The photo was captured at an angle:
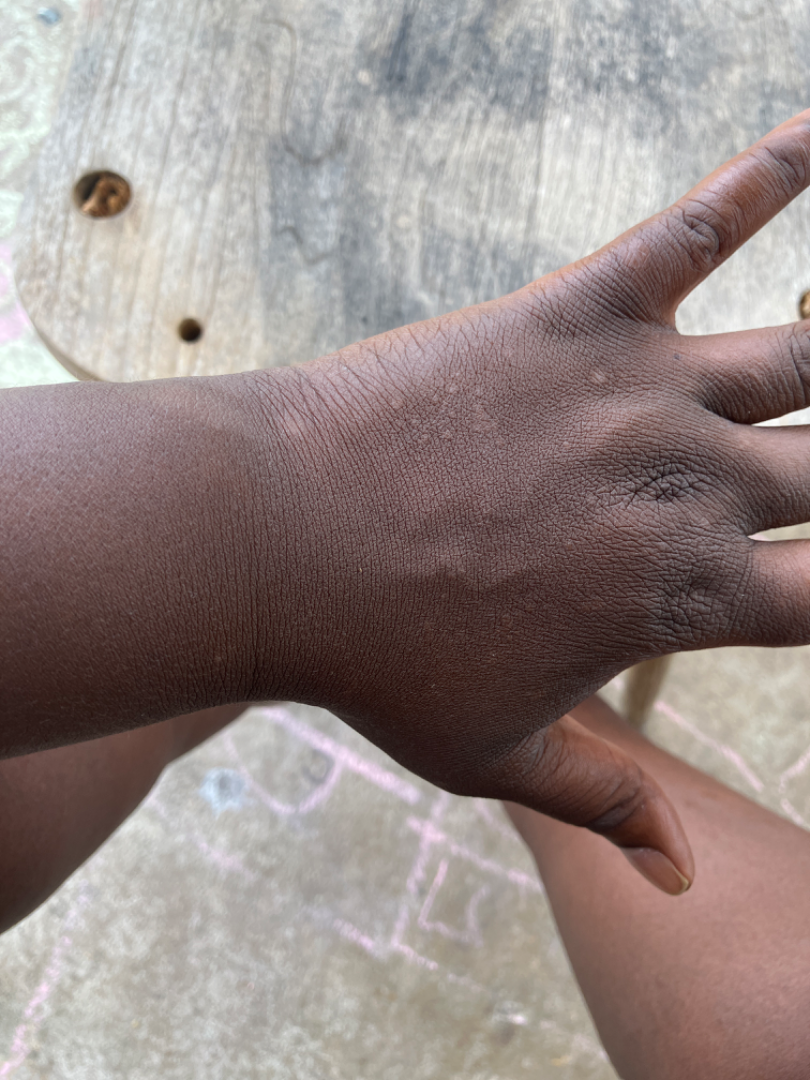One reviewing dermatologist: the impression was split between Chronic dermatitis, NOS and Allergic Contact Dermatitis.